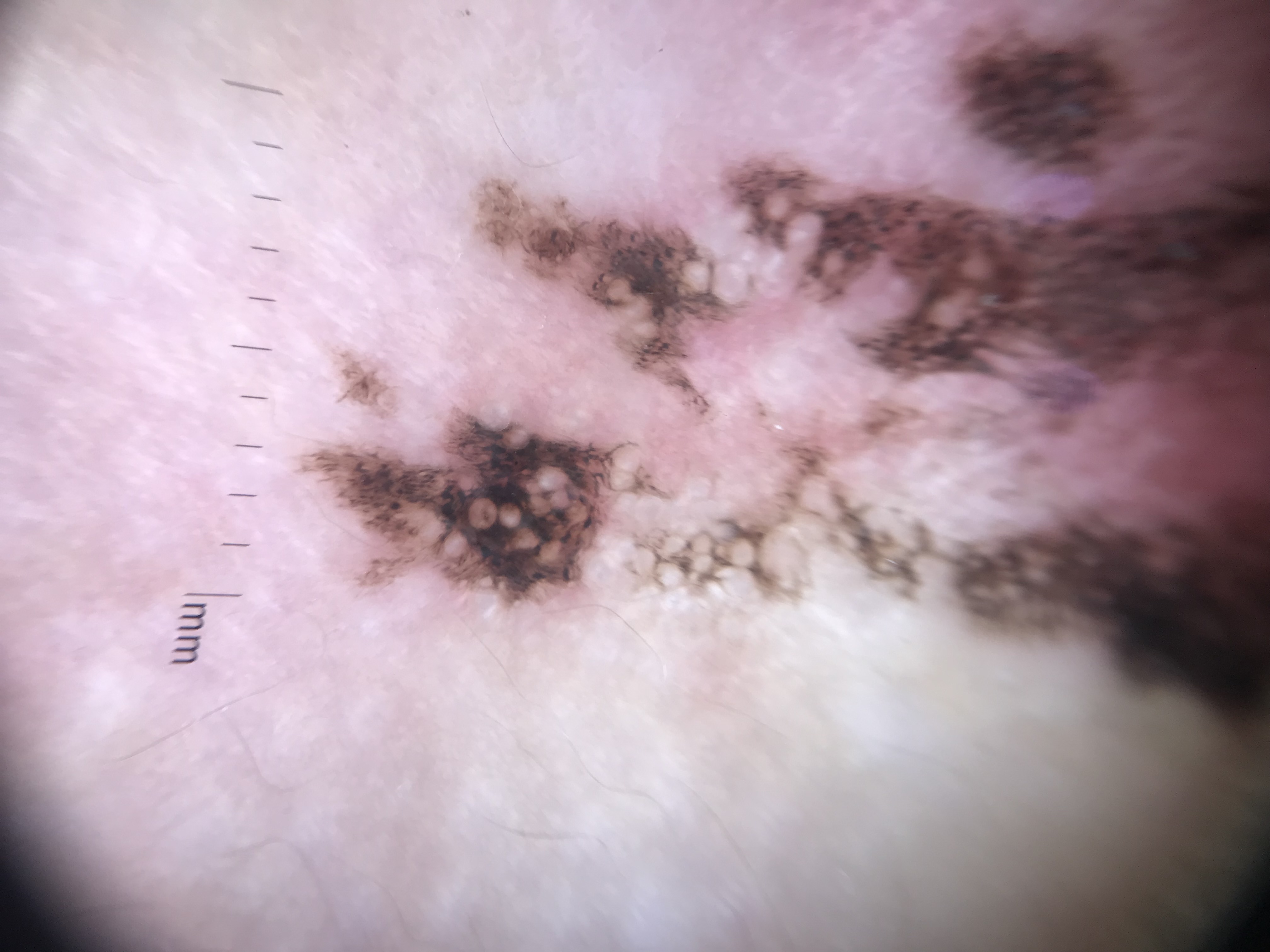Histopathologically confirmed as a melanoma.